The patient is Fitzpatrick III · a contact-polarized dermoscopy image of a skin lesion · the chart notes no first-degree relative with melanoma and no previous melanoma · a female patient in their 30s:
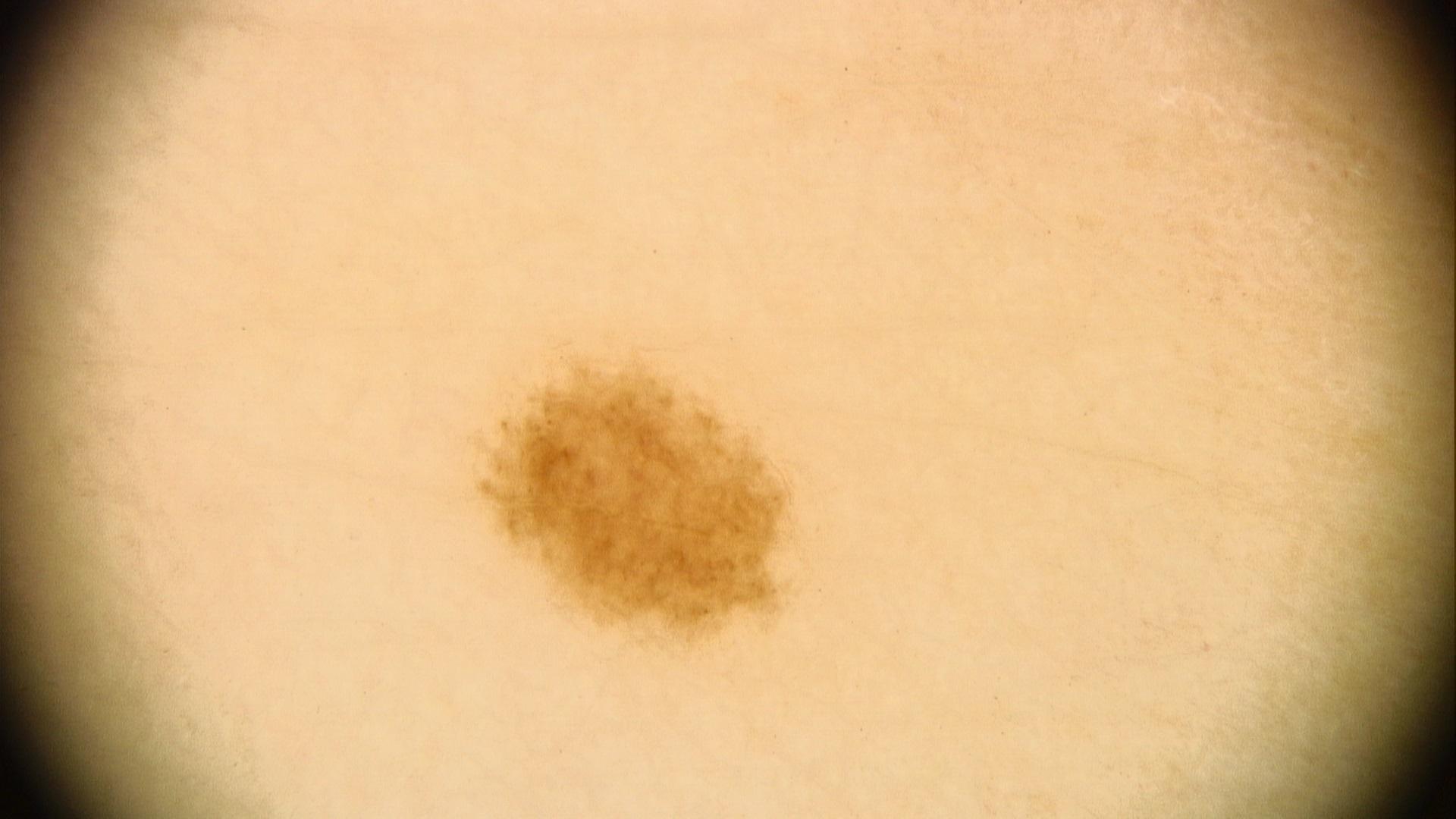{"lesion_location": {"region": "a lower extremity"}, "diagnosis": {"name": "Nevus", "malignancy": "benign", "confirmation": "expert clinical impression", "lineage": "melanocytic"}}